A skin lesion imaged with a dermatoscope.
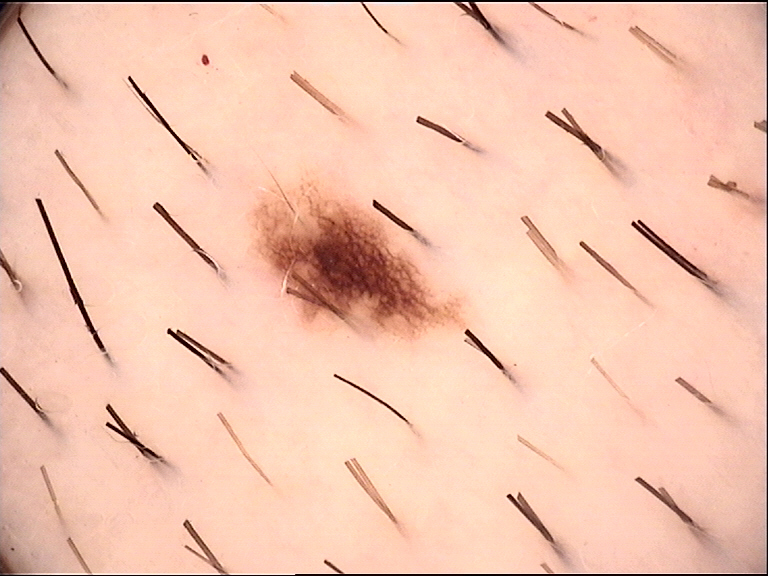Diagnosed as a benign lesion — a dysplastic junctional nevus.